The patient is 50–59, female; this image was taken at an angle; located on the top or side of the foot, leg, back of the torso and arm.
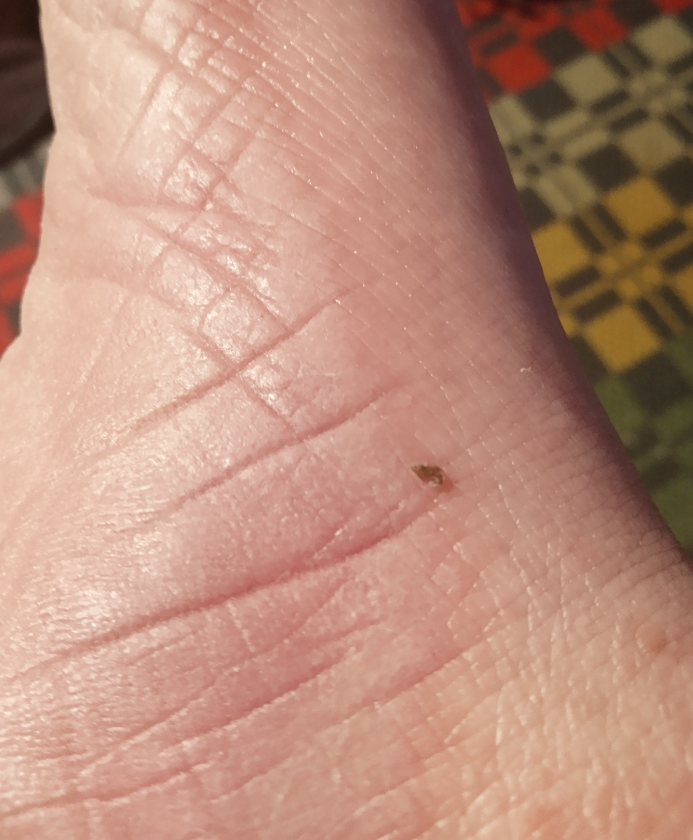diagnostic considerations — Keratoderma (favored); Hyperkeratosis (possible).